The photograph is a close-up of the affected area.
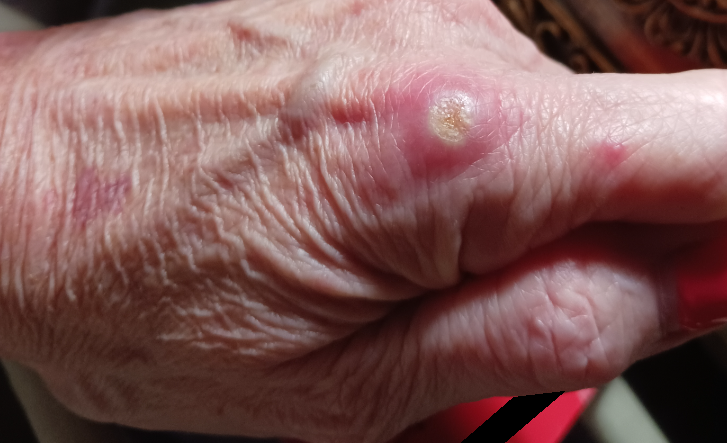Q: What is the lesion texture?
A: raised or bumpy
Q: What is the differential diagnosis?
A: most consistent with SCC/SCCIS; also raised was Abscess; with consideration of Cyst